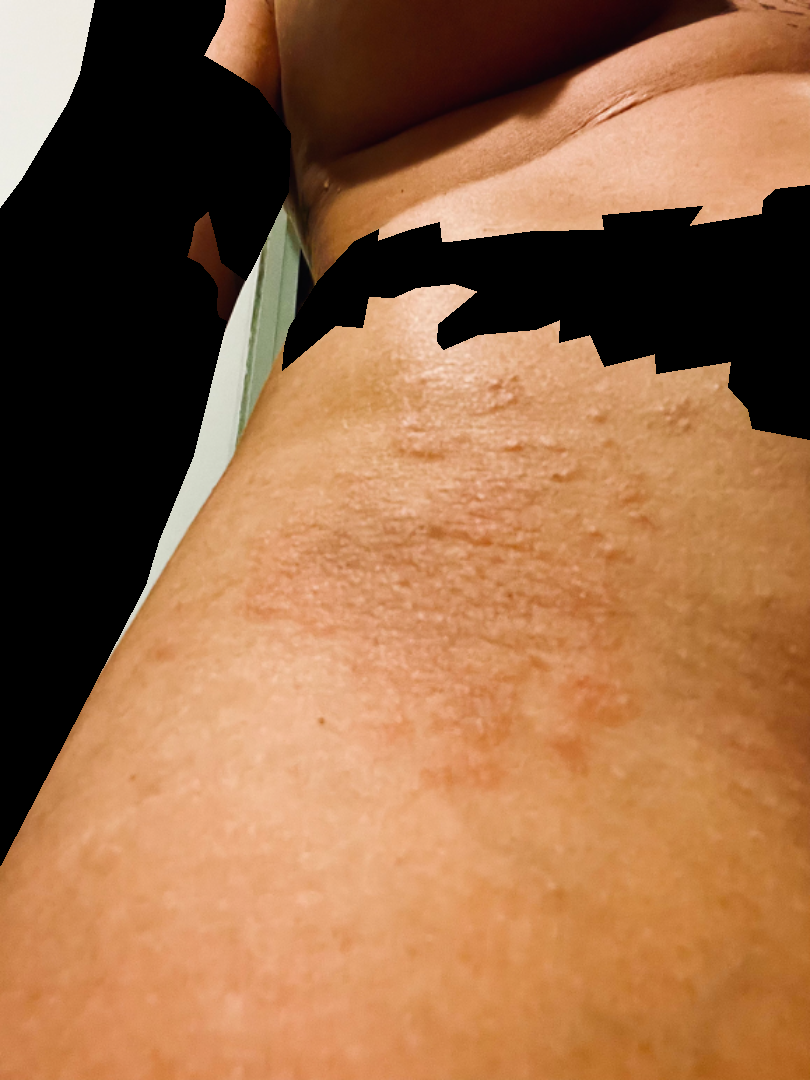Q: What was the assessment?
A: unable to determine
Q: Patient's own categorization?
A: a rash
Q: Reported symptoms?
A: itching and bothersome appearance
Q: What is the lesion texture?
A: raised or bumpy
Q: Where on the body?
A: front of the torso
Q: Image view?
A: close-up
Q: Any systemic symptoms?
A: mouth sores, joint pain and fatigue
Q: Age and sex?
A: female, age 30–39